The contributor notes the condition has been present for one to four weeks; the photograph was taken at a distance; no associated systemic symptoms reported; the contributor notes the lesion is raised or bumpy:
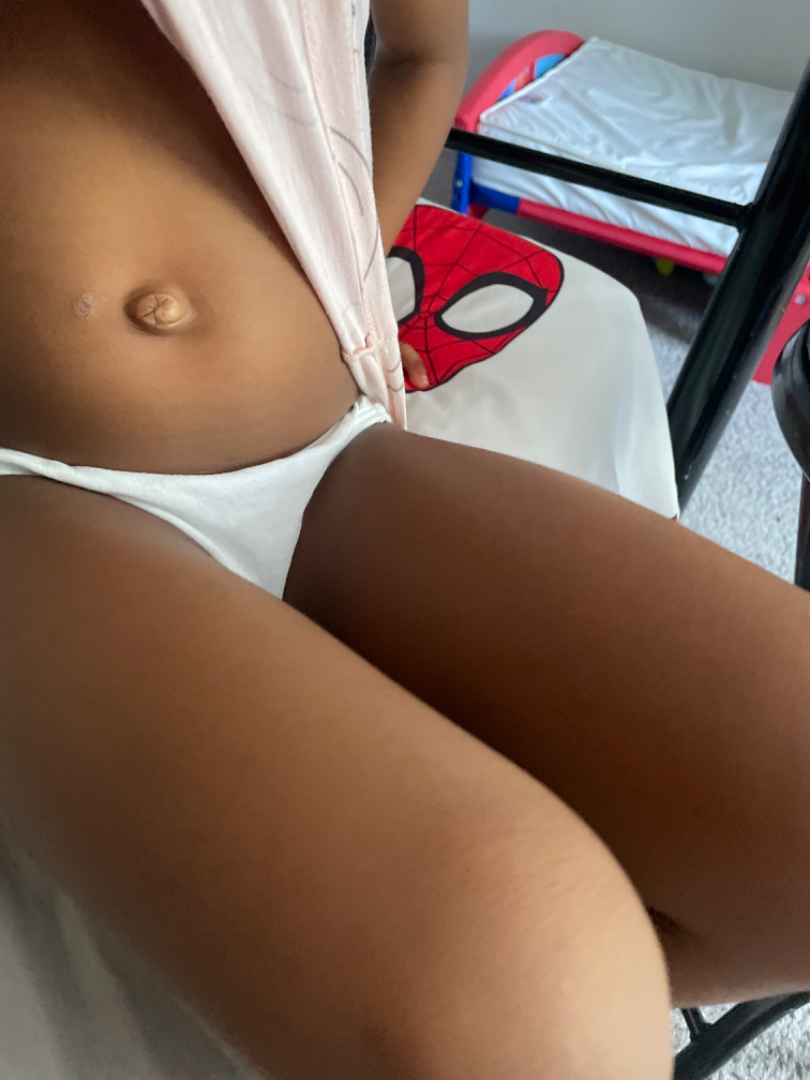{
  "assessment": "ungradable on photographic review"
}